Located on the back of the torso · this image was taken at a distance: 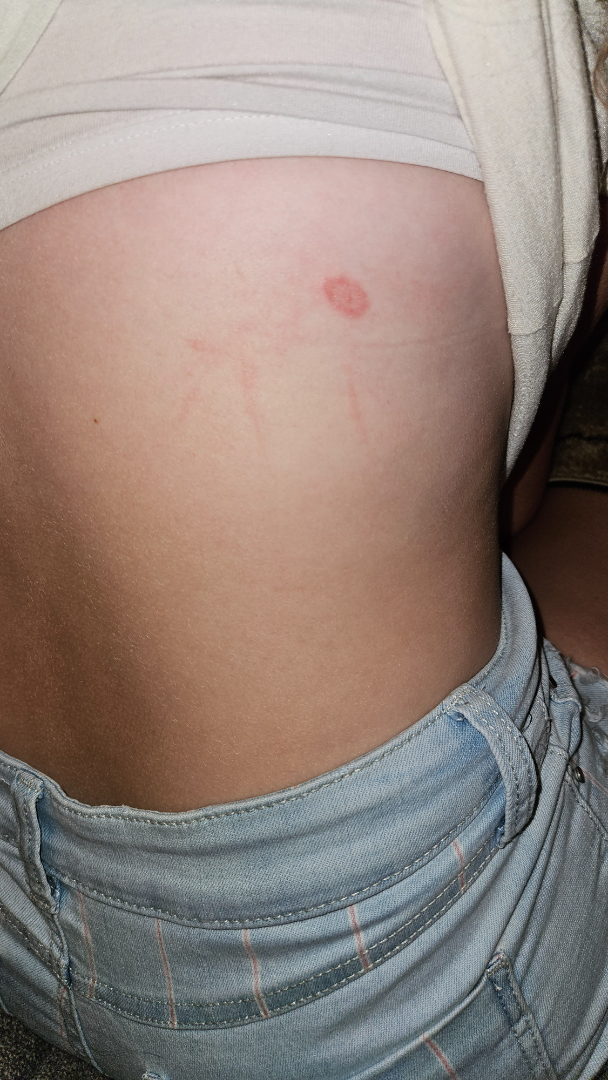self-categorized as=a rash | patient-reported symptoms=bothersome appearance | history=one to four weeks | surface texture=flat | skin tone=FST II; lay graders estimated Monk Skin Tone 2 or 3 (two reviewer pools) | differential=most consistent with Tinea.